A skin lesion imaged with a dermatoscope. A female subject, aged 38-42.
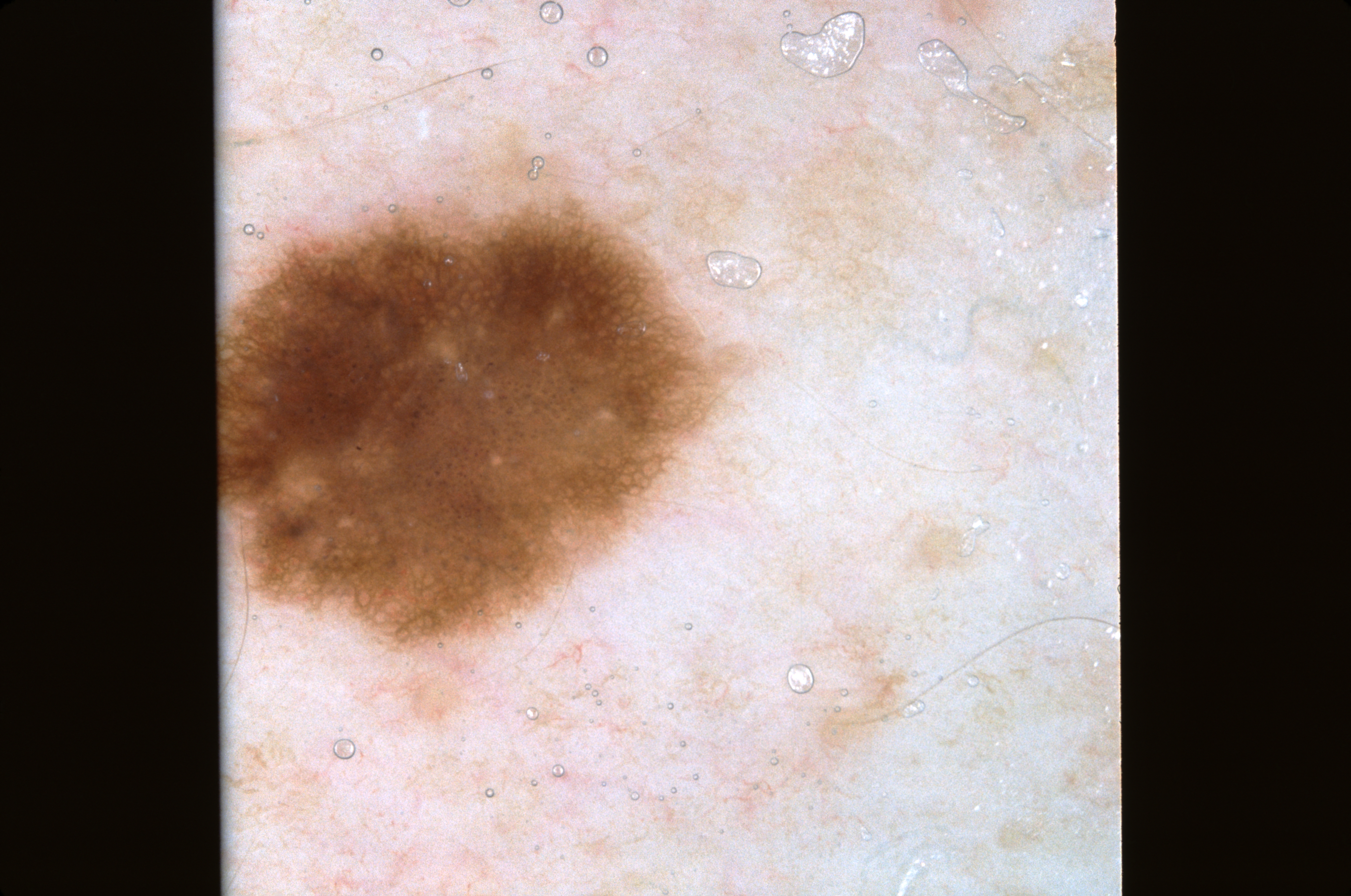Dermoscopic review identifies pigment network, with no milia-like cysts, negative network, or streaks. With coordinates (x1, y1, x2, y2), the lesion occupies the region bbox(216, 157, 770, 650). A moderately sized lesion. The lesion was assessed as a melanocytic nevus, a benign lesion.